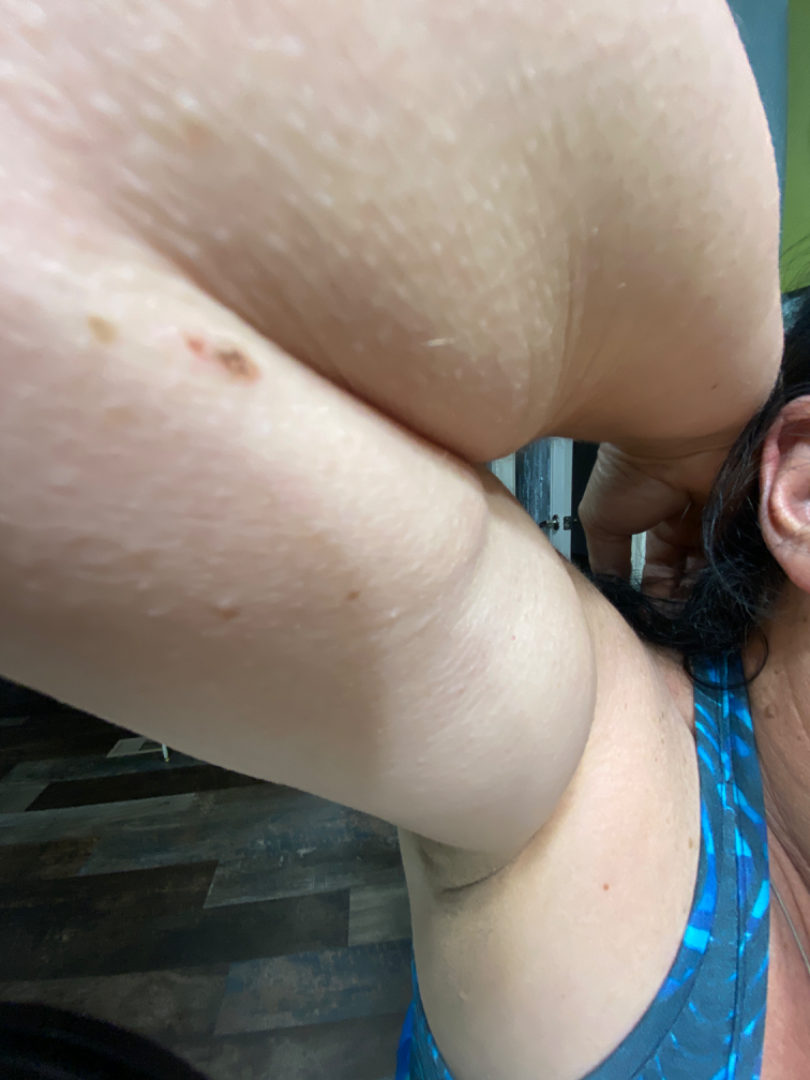{"assessment": "indeterminate from the photograph", "texture": ["rough or flaky", "raised or bumpy"], "body_site": "arm", "patient": "female, age 50–59", "shot_type": "close-up", "symptoms": ["darkening", "bothersome appearance", "itching"], "patient_category": "a growth or mole", "skin_tone": {"fitzpatrick": "III", "monk_skin_tone": 2}}